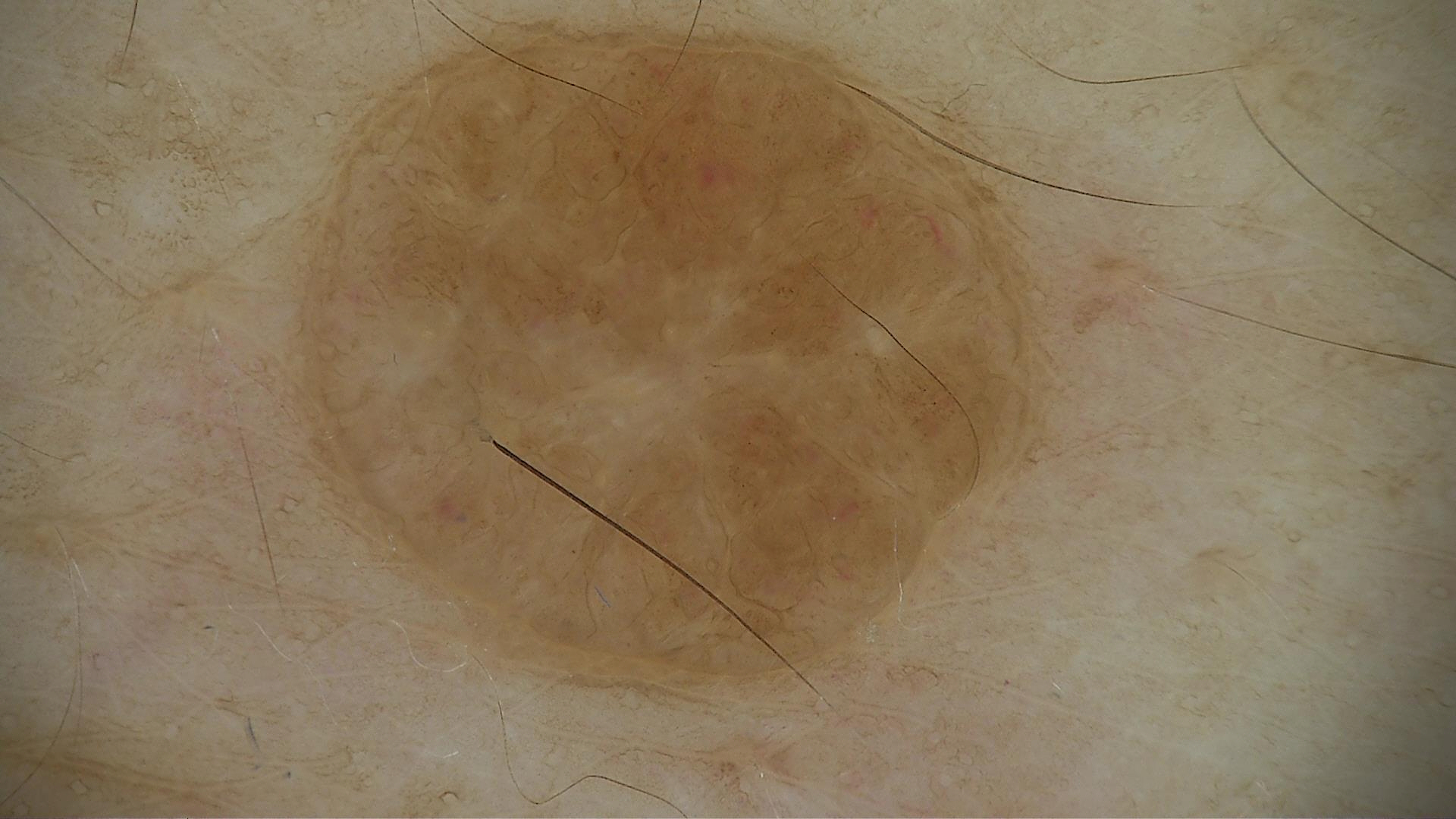| feature | finding |
|---|---|
| category | banal |
| diagnosis | dermal nevus (expert consensus) |